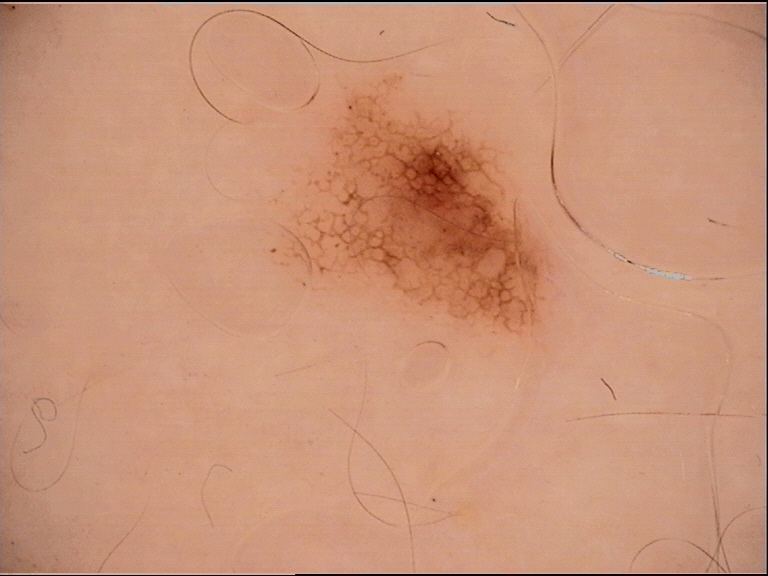The diagnosis was a benign lesion — a dysplastic junctional nevus.